A dermoscopy image of a single skin lesion — 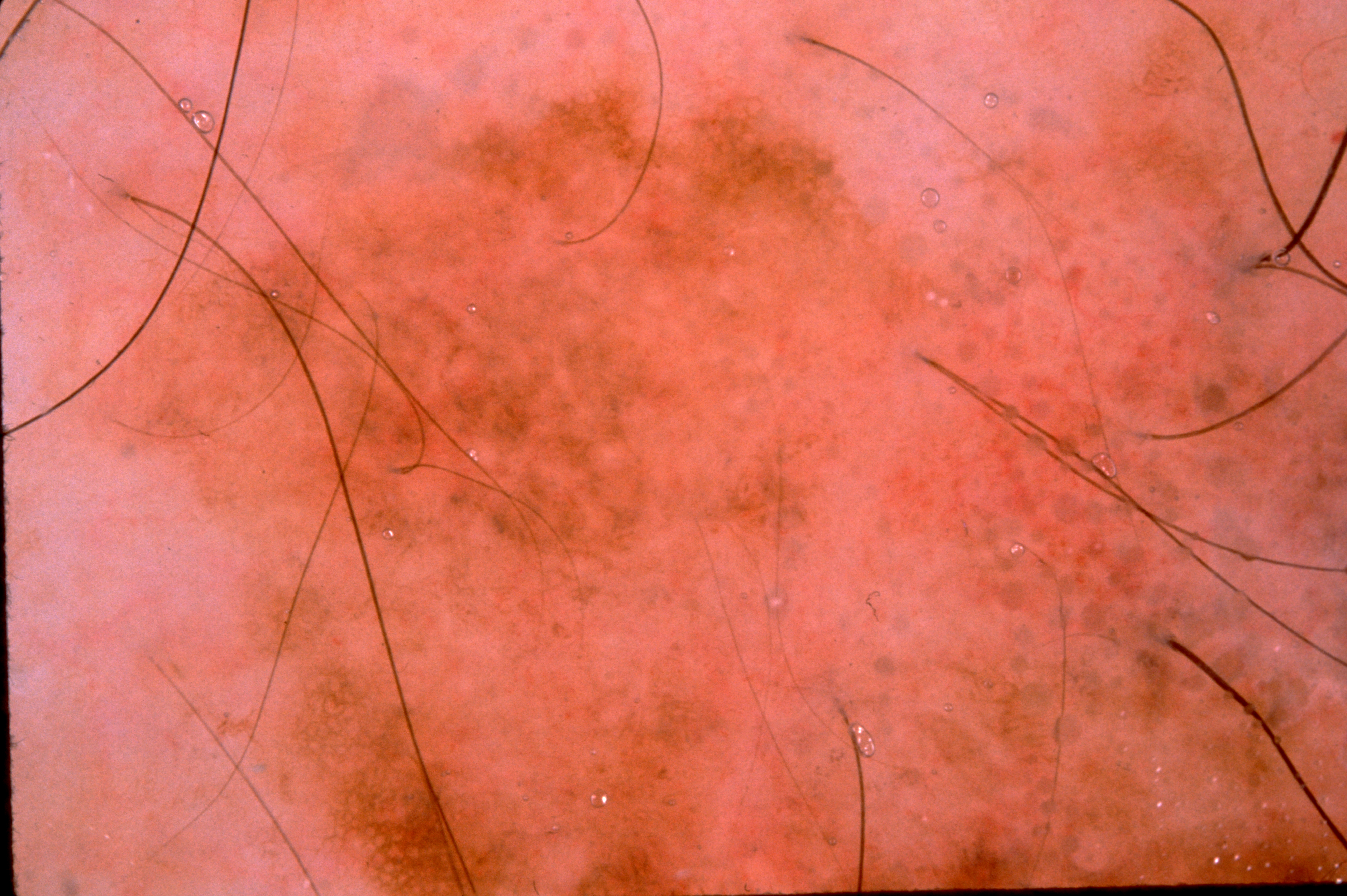The dermoscopic pattern shows pigment network; no streaks, negative network, or milia-like cysts. The lesion spans essentially the entire dermoscopic field. The lesion was assessed as a melanocytic nevus, a benign skin lesion.